Symptoms reported: bleeding, itching and darkening · the contributor is 18–29, female · the patient reports the lesion is raised or bumpy and rough or flaky · an image taken at a distance.
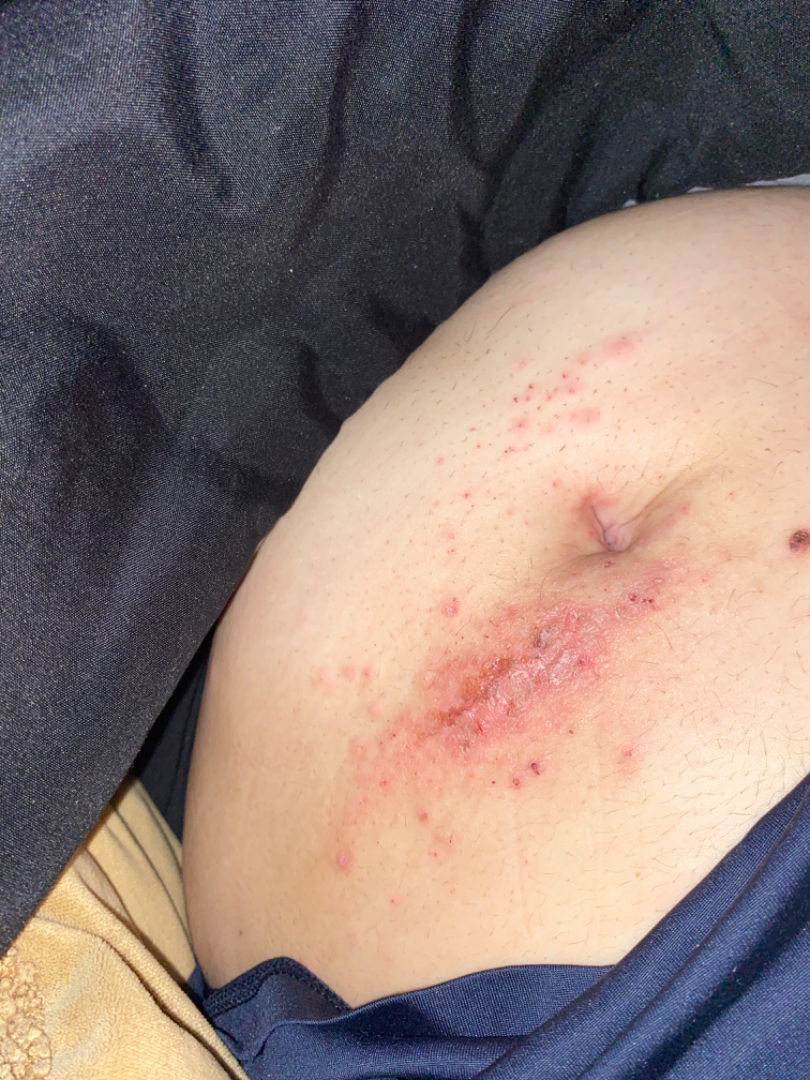{"differential": {"leading": ["Allergic Contact Dermatitis"], "considered": ["Irritant Contact Dermatitis"]}}